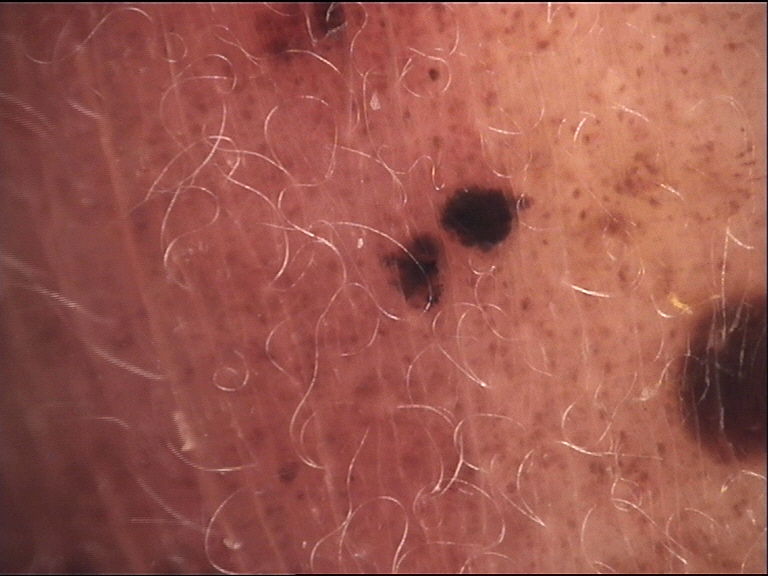Q: What is the diagnosis?
A: congenital compound nevus (expert consensus)